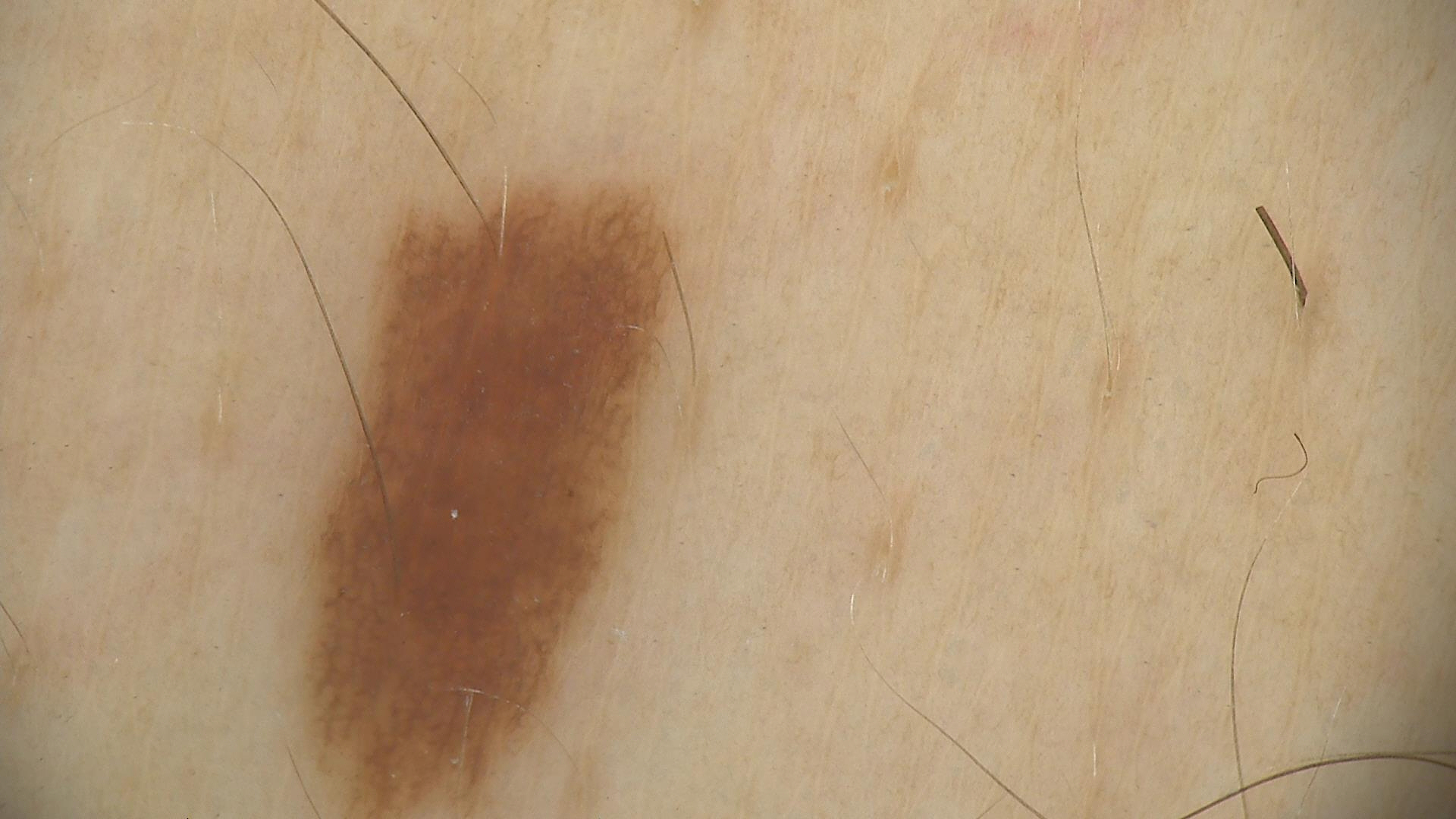• imaging: dermoscopy
• diagnosis: dysplastic junctional nevus (expert consensus)